Acquired for a research image collection, with no referral diagnosis; a skin lesion imaged with a dermatoscope; on a questionnaire the patient reported a personal history of skin cancer and a personal history of cancer; the patient says their skin tans without first burning; the patient describes having a moderate number of moles:
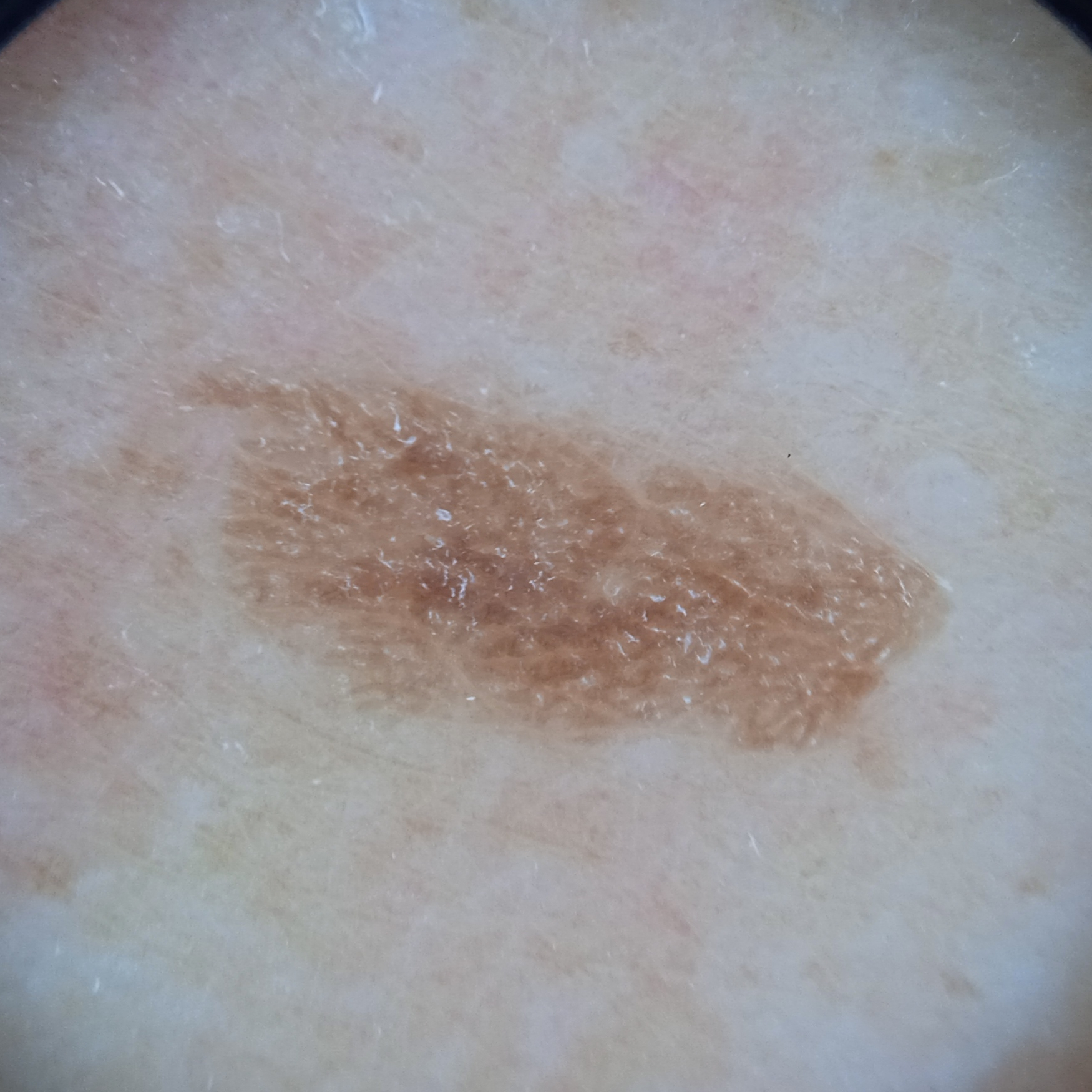location: the back; lesion size: 8.4 mm; diagnostic label: seborrheic keratosis (dermatologist consensus).